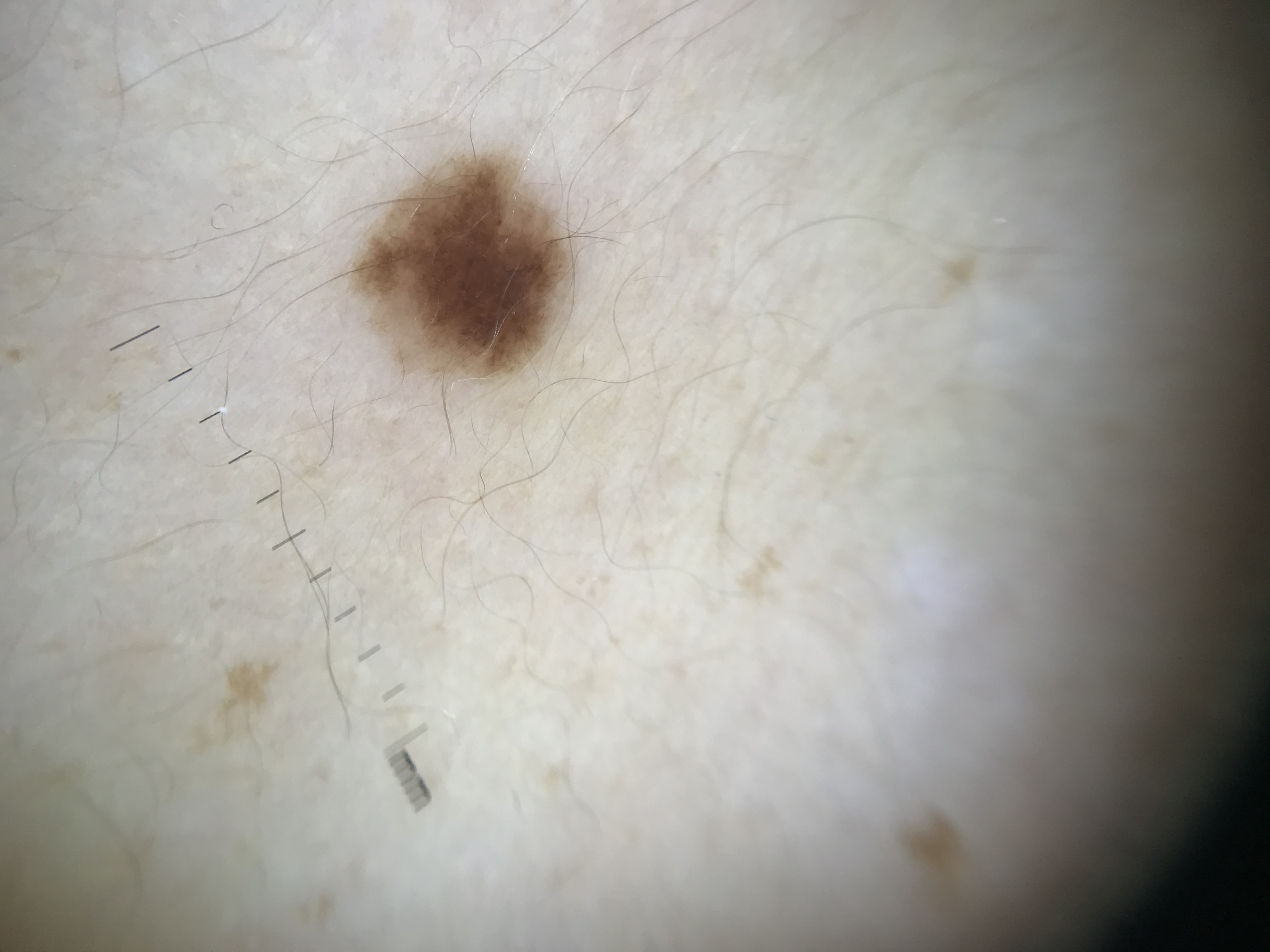  image: dermoscopy
  diagnosis:
    name: junctional nevus
    code: jb
    malignancy: benign
    super_class: melanocytic
    confirmation: expert consensus